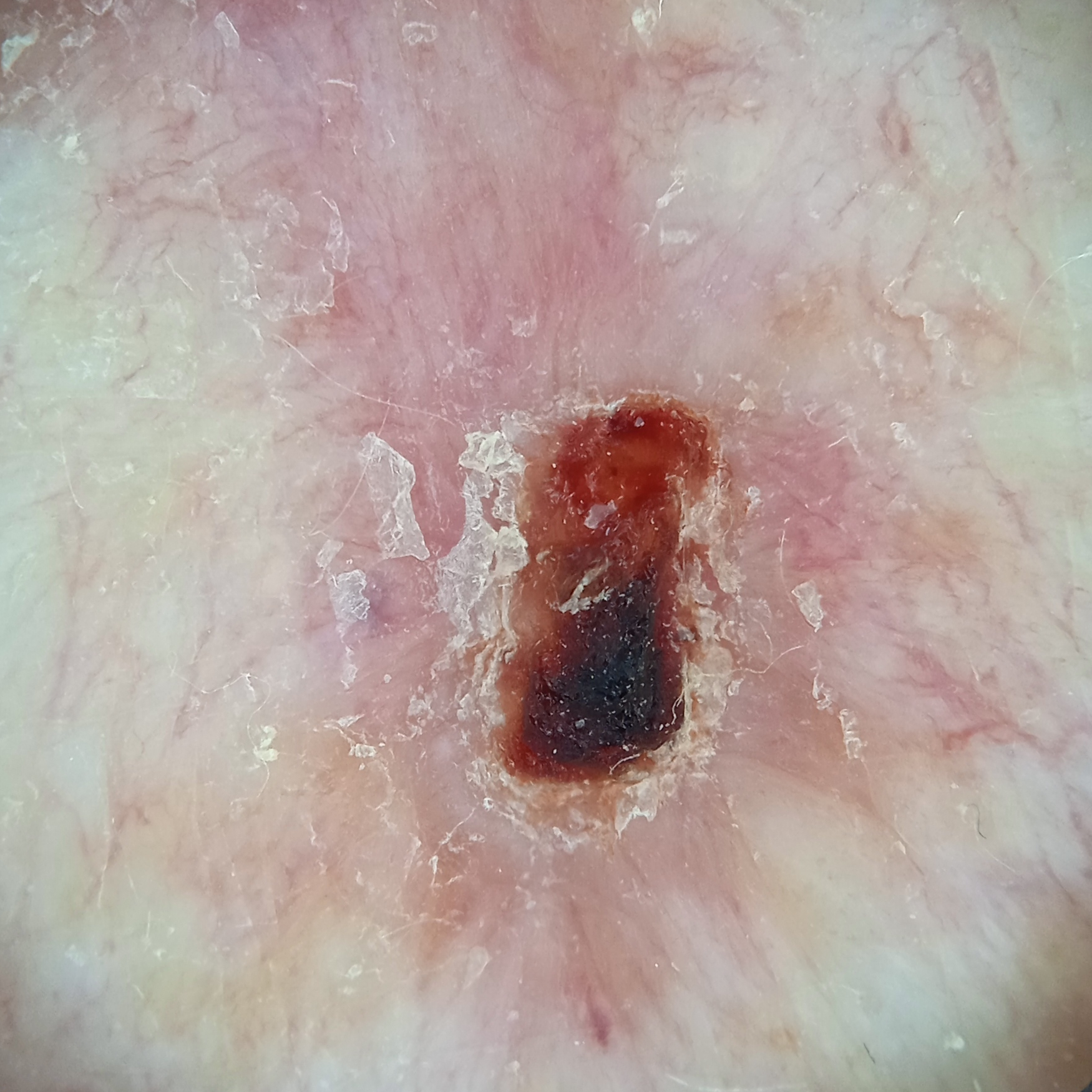Clinical context:
A male patient 83 years old. Collected as part of a research study, without a referral diagnosis. The lesion involves the back. Measuring roughly 9.5 mm.
Conclusion:
The lesion was assessed as a basal cell carcinoma.